The lesion involves the leg. A close-up photograph. The contributor is 40–49, female:
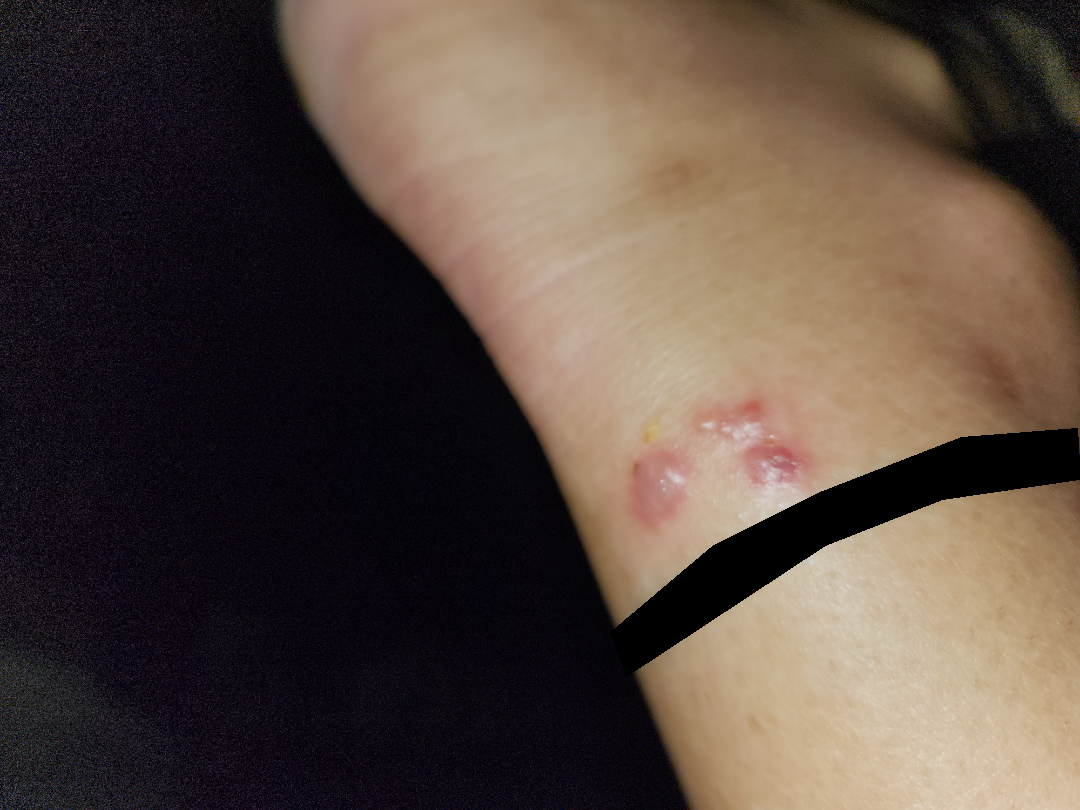The contributor reports itching and bothersome appearance. The patient described the issue as a rash. Texture is reported as raised or bumpy and fluid-filled. The differential includes Herpes Zoster, Impetigo and Allergic Contact Dermatitis, with no clear leading consideration.